Located on the arm, head or neck and leg. Female patient, age 60–69. This is a close-up image: 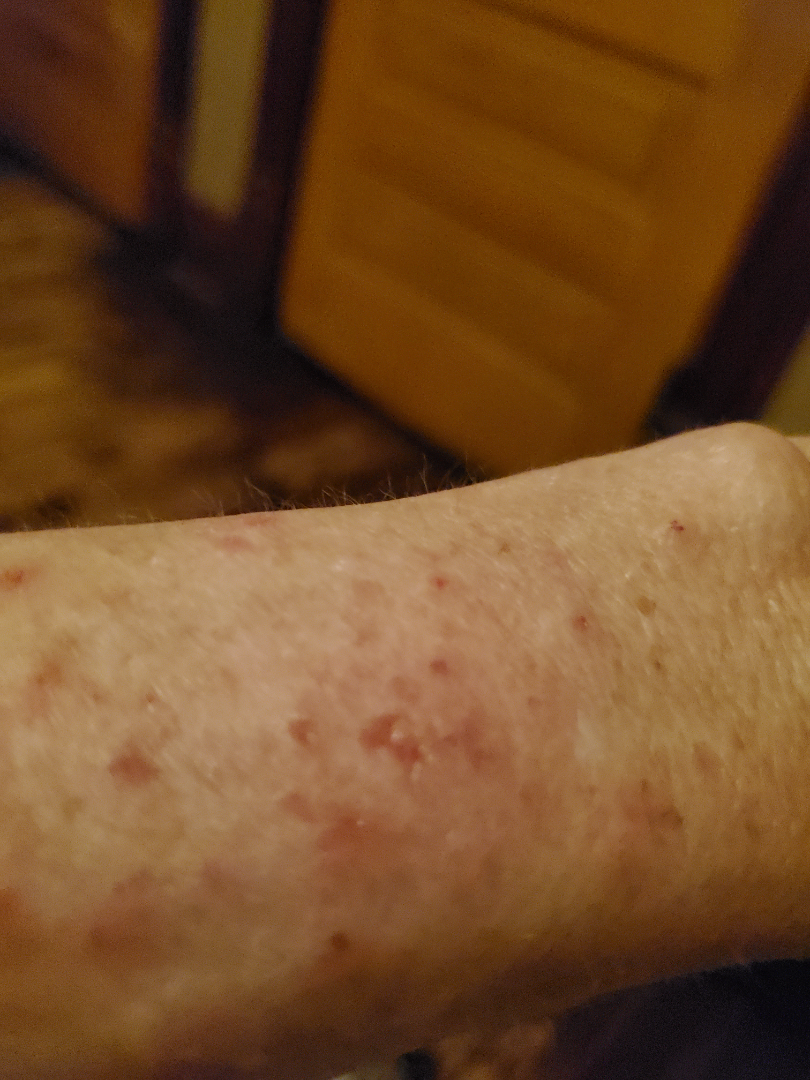No differential diagnosis could be assigned on photographic review.